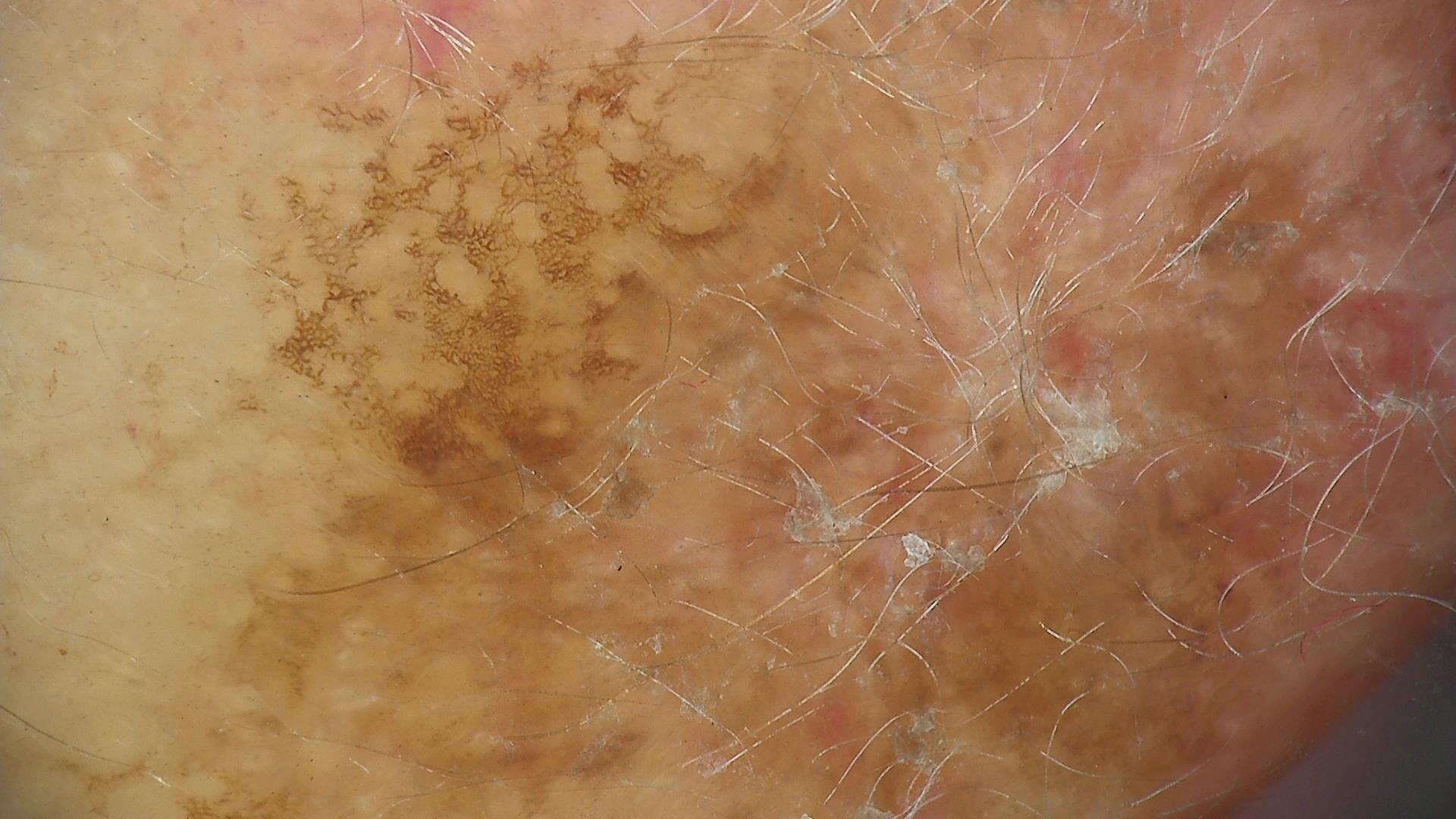Case: A skin lesion imaged with a dermatoscope. This is a keratinocytic lesion. Impression: Consistent with a benign lesion — a seborrheic keratosis.